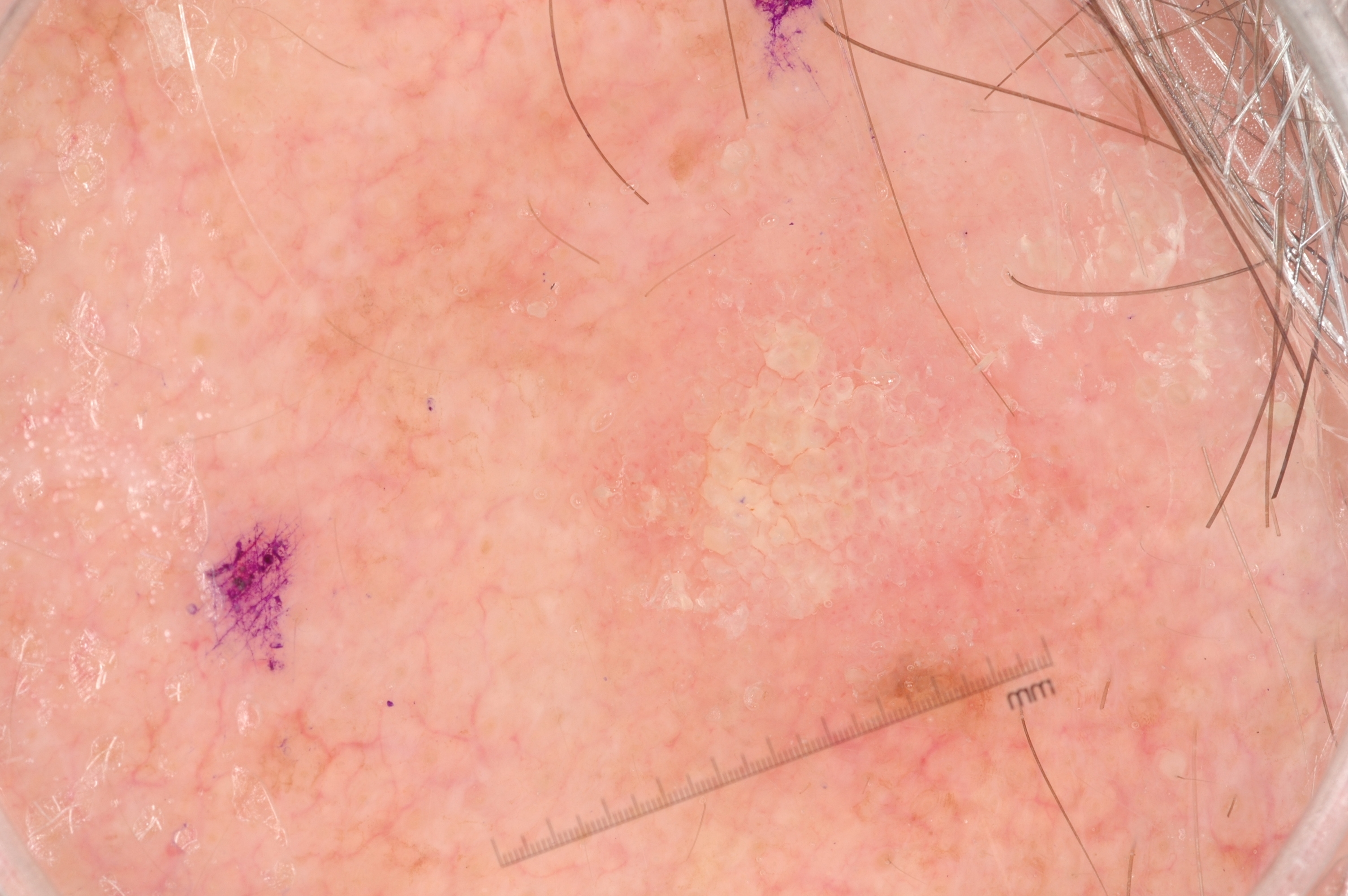image = dermoscopic image
patient = male, aged approximately 60
bounding box = 521 189 1102 729
dermoscopic features assessed but absent = negative network, streaks, pigment network, and milia-like cysts
diagnosis = a seborrheic keratosis, a benign skin lesion